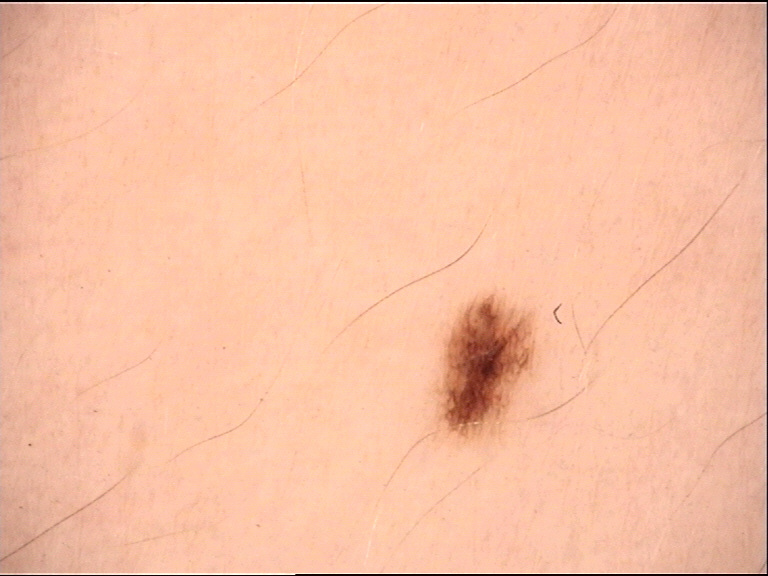<lesion>
<diagnosis>
<name>dysplastic junctional nevus</name>
<code>jd</code>
<malignancy>benign</malignancy>
<super_class>melanocytic</super_class>
<confirmation>expert consensus</confirmation>
</diagnosis>
</lesion>